The photograph was taken at a distance; the affected area is the back of the hand; reported duration is less than one week: 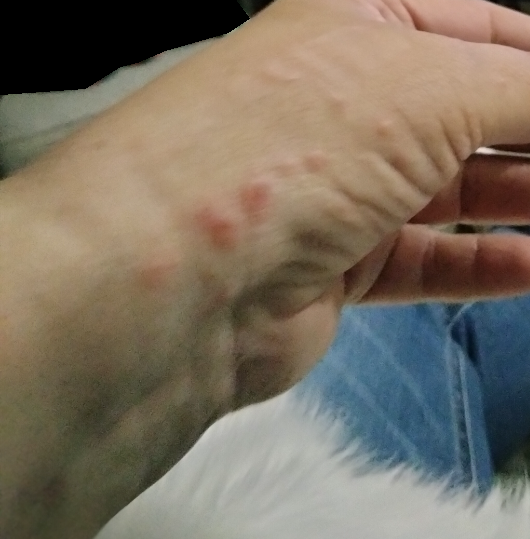<report>
  <differential>
    <leading>Insect Bite</leading>
    <considered>Urticaria, Allergic Contact Dermatitis</considered>
  </differential>
</report>